A dermoscopic close-up of a skin lesion: 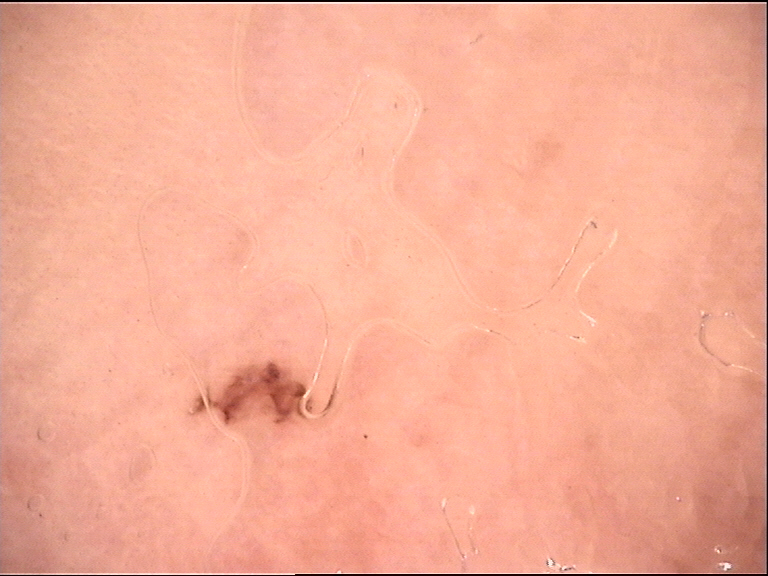Conclusion: The diagnosis was a benign lesion — a dysplastic junctional nevus.